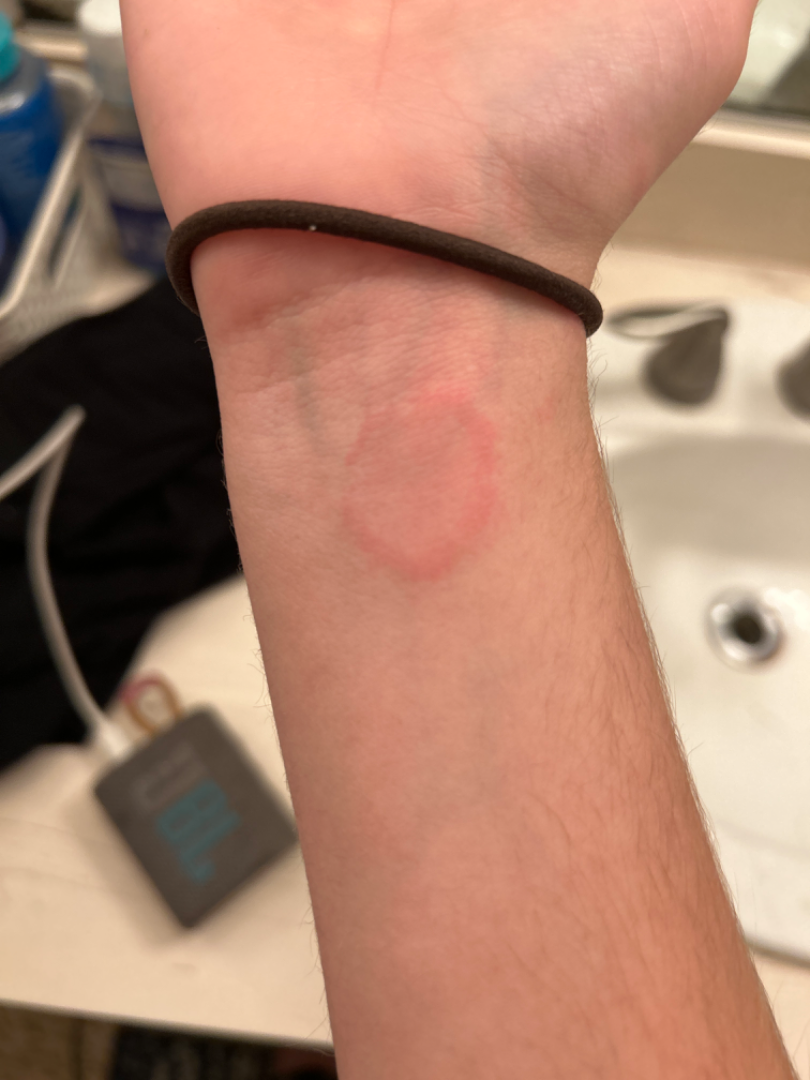Notes:
– assessment: unable to determine
– skin tone: Fitzpatrick II; human graders estimated MST 2–3
– symptoms: itching
– present for: less than one week
– anatomic site: front of the torso, leg, arm and top or side of the foot
– lesion texture: raised or bumpy
– photo taken: close-up